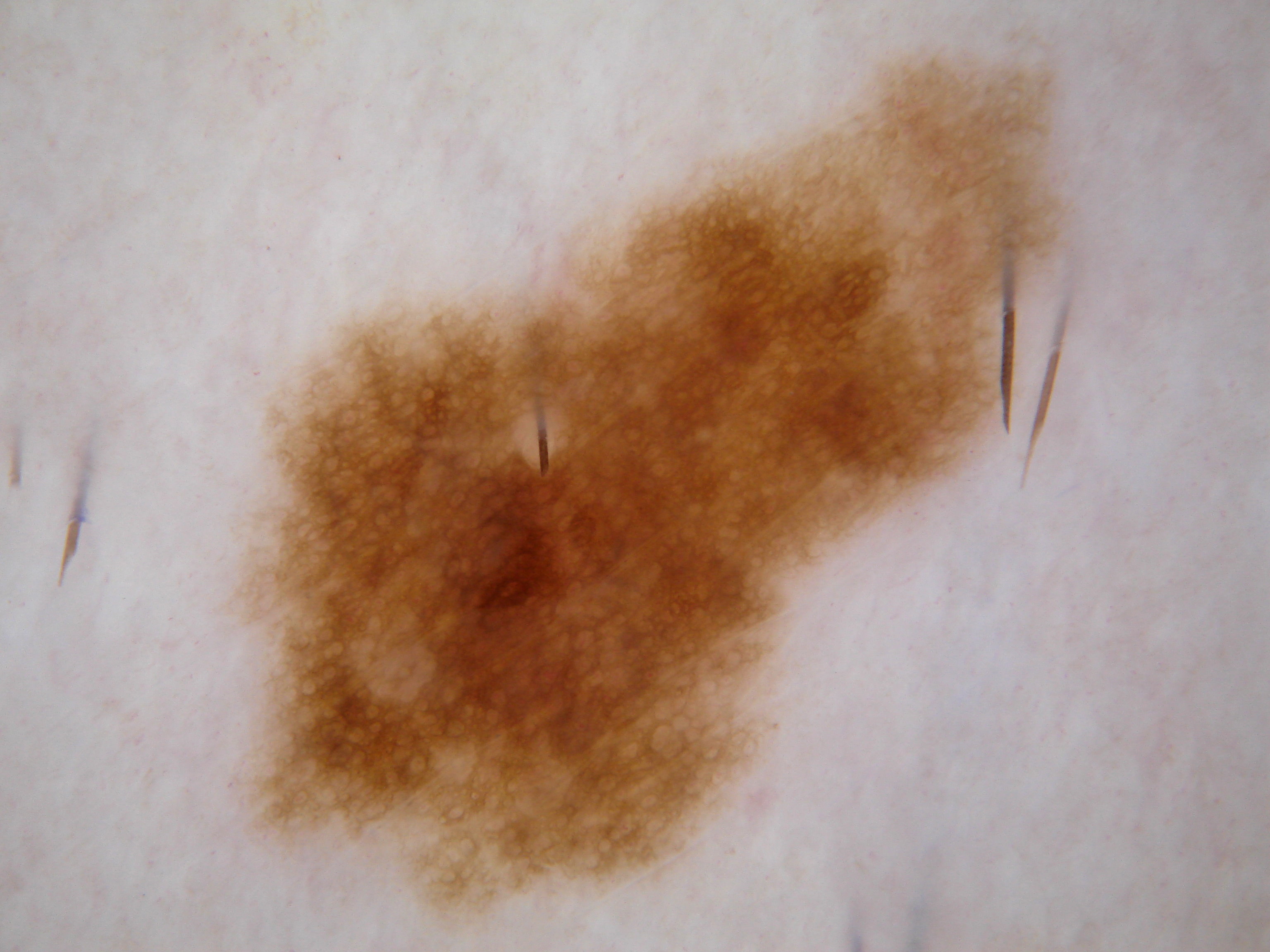Image and clinical context: Dermoscopy of a skin lesion. The visible lesion spans x1=244, y1=59, x2=1068, y2=915. A large lesion occupying much of the field. Dermoscopic assessment notes pigment network, with no streaks, globules, negative network, or milia-like cysts. Assessment: Clinically diagnosed as a melanocytic nevus, a benign lesion.